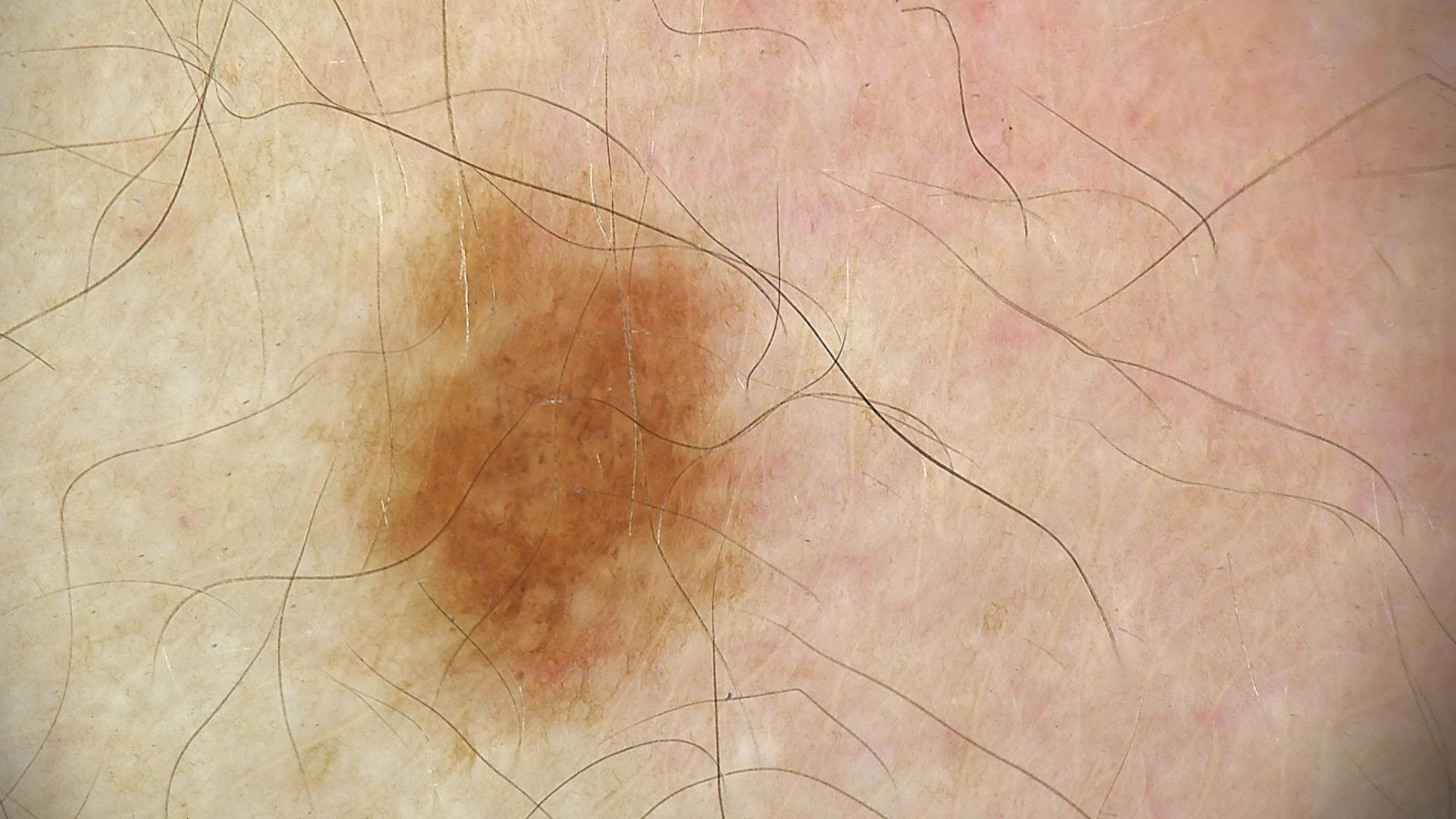label — dysplastic junctional nevus (expert consensus).